A female patient aged around 85 or older. The patient was assessed as Fitzpatrick II. A contact-polarized dermoscopy image of a skin lesion.
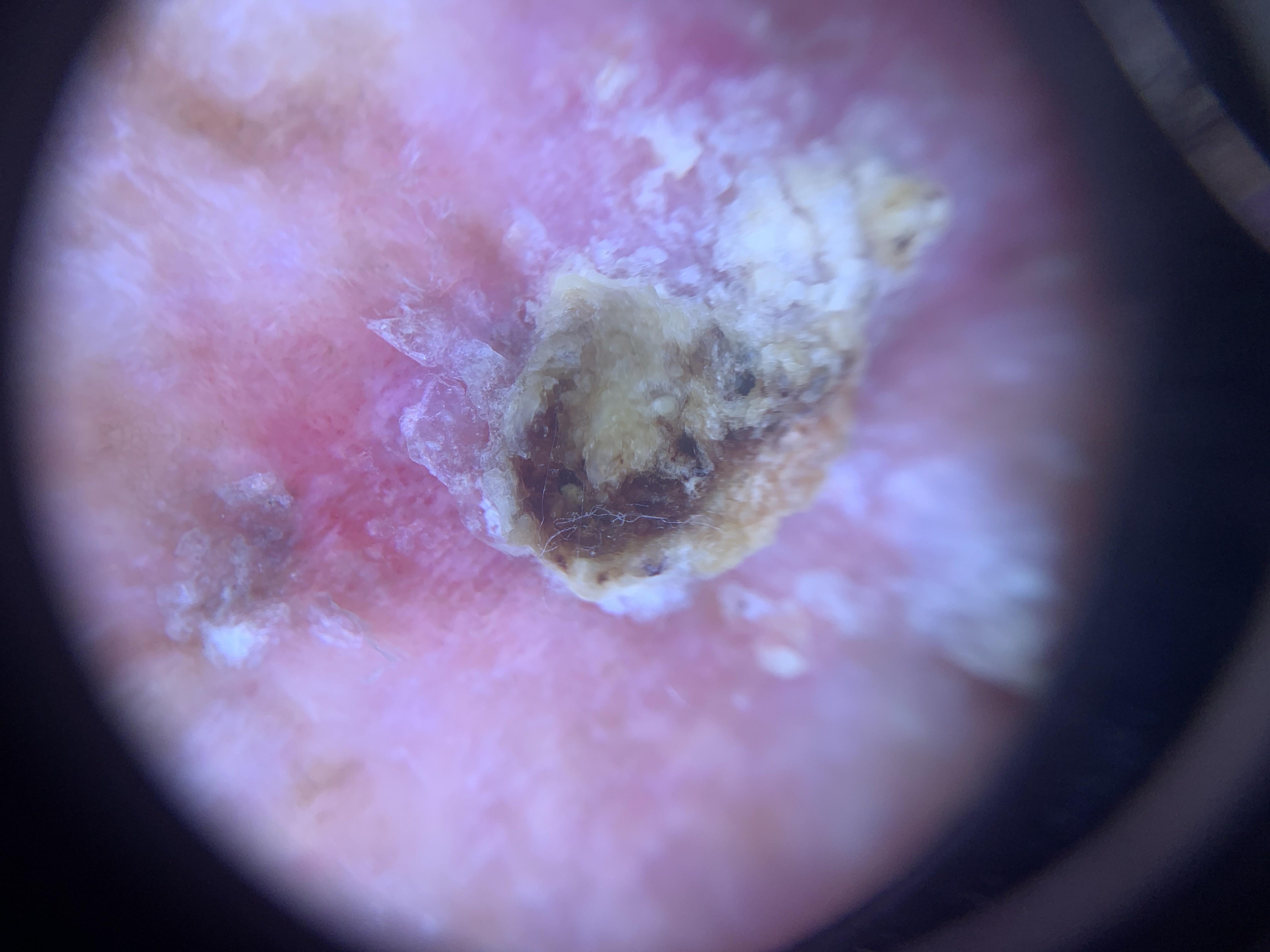Located on a lower extremity. Biopsy-confirmed as a malignant, epidermal lesion — a squamous cell carcinoma.